The lesion involves the leg · the lesion is associated with itching · female contributor, age 70–79 · Fitzpatrick skin type I; lay reviewers estimated MST 3 (US pool) or 2 (India pool) · present for about one day · an image taken at an angle · texture is reported as raised or bumpy:
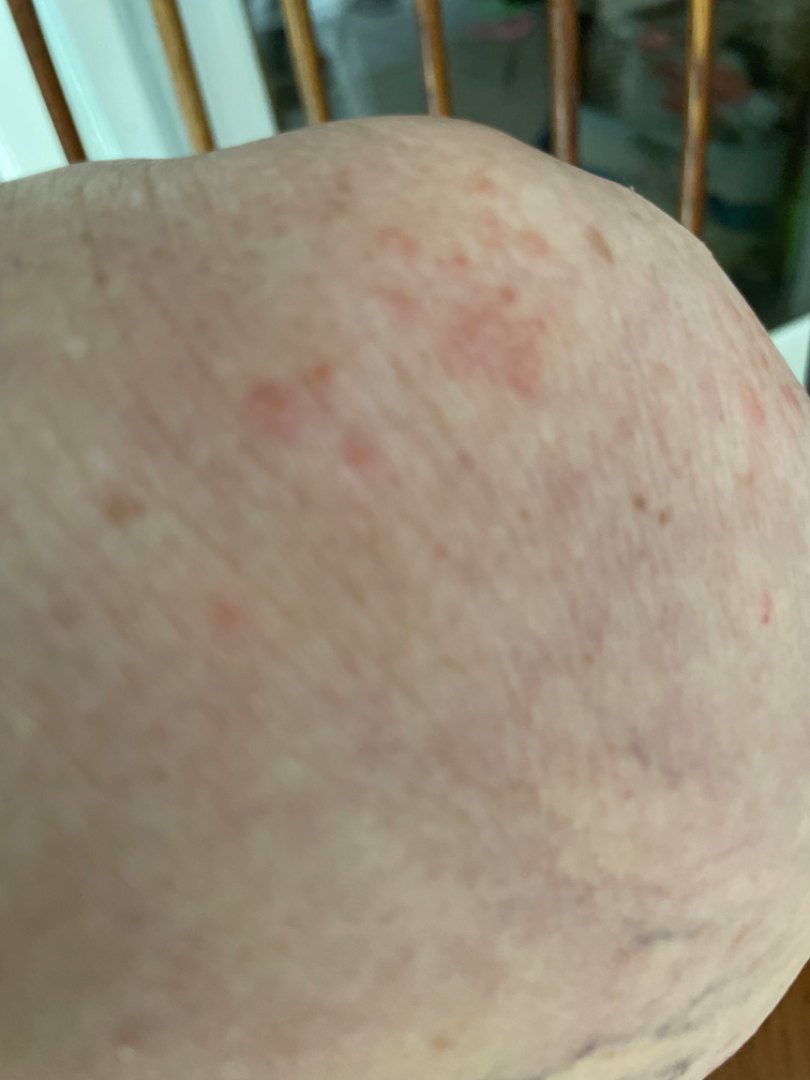Review: On photographic review: the differential is split between Psoriasis, Eczema and Dermatitis herpetiformis.